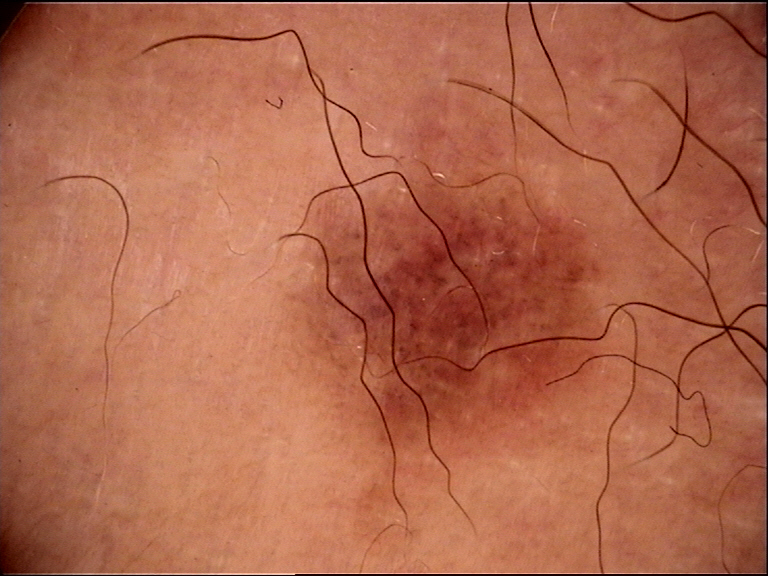Q: What kind of image is this?
A: dermatoscopy
Q: What was the diagnostic impression?
A: dysplastic compound nevus (expert consensus)